The patient says their skin tans without first burning; few moles overall by the patient's own estimate; on a questionnaire the patient reported a personal history of cancer and a personal history of skin cancer — 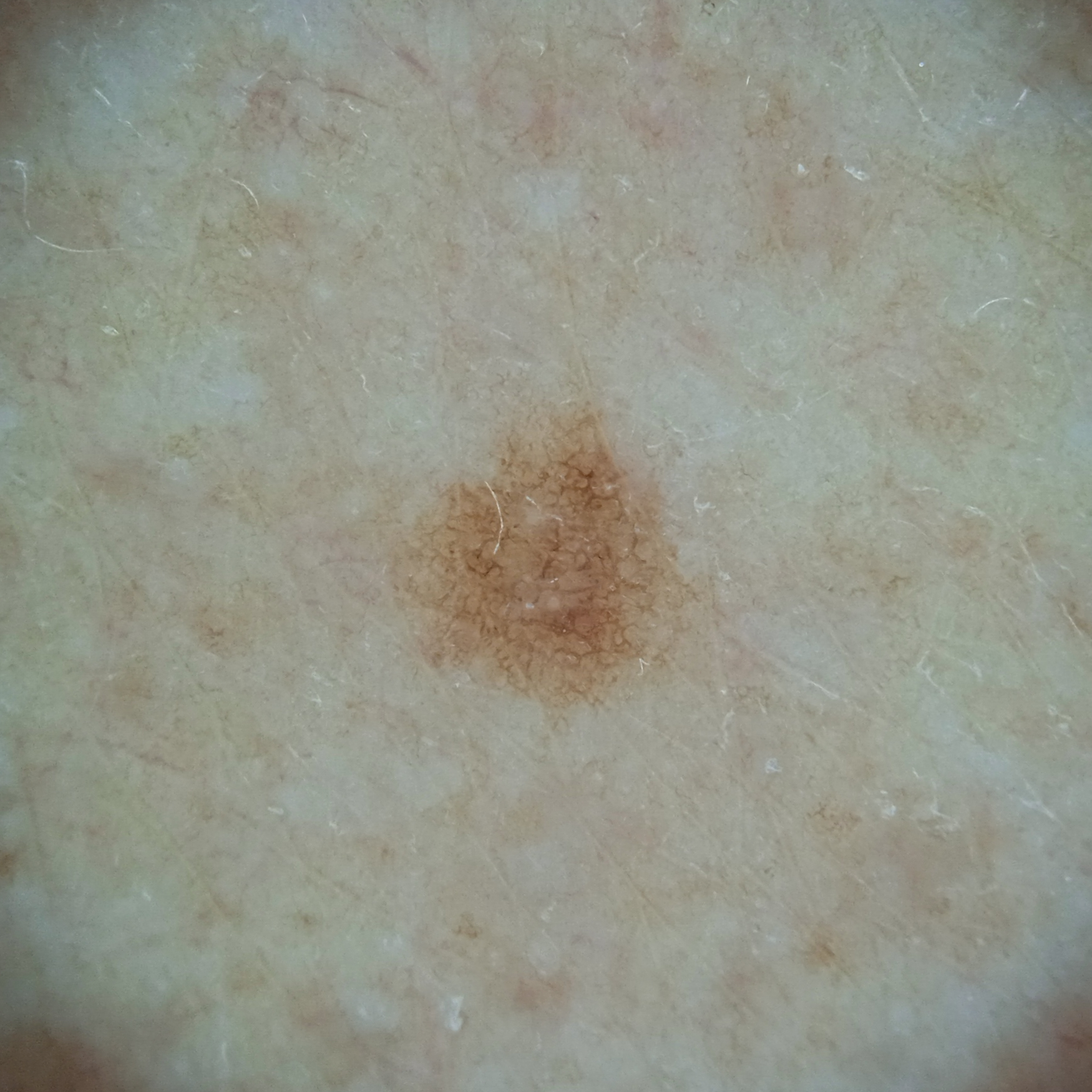Findings:
* lesion size: 2.8 mm
* assessment: melanocytic nevus (dermatologist consensus)